A skin lesion imaged with a dermatoscope: 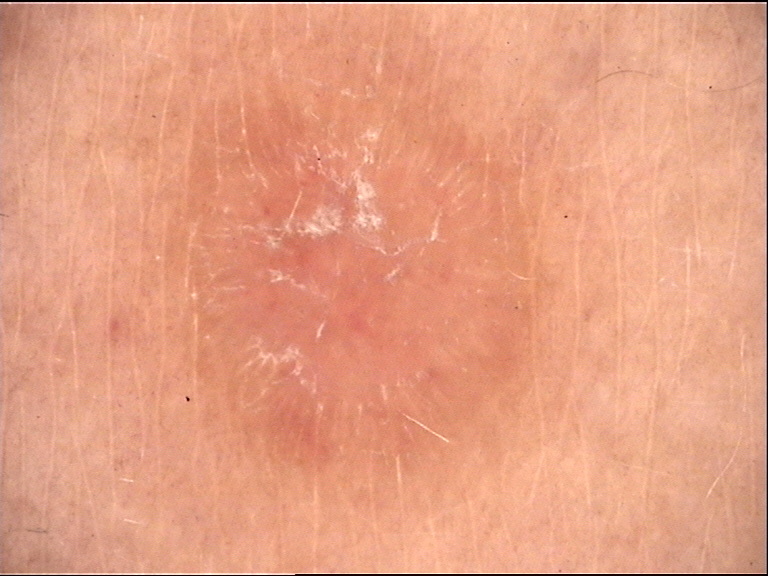The morphology is that of a fibro-histiocytic lesion. Labeled as a benign lesion — a dermatofibroma.